The photograph was taken at an angle. Located on the front of the torso and head or neck. The patient also reports fatigue and shortness of breath. The patient described the issue as a rash. The patient is a male aged 50–59 — 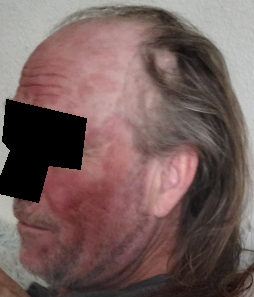Impression: Favoring Seborrheic Dermatitis; a remote consideration is Psoriasis; less probable is Eczema.